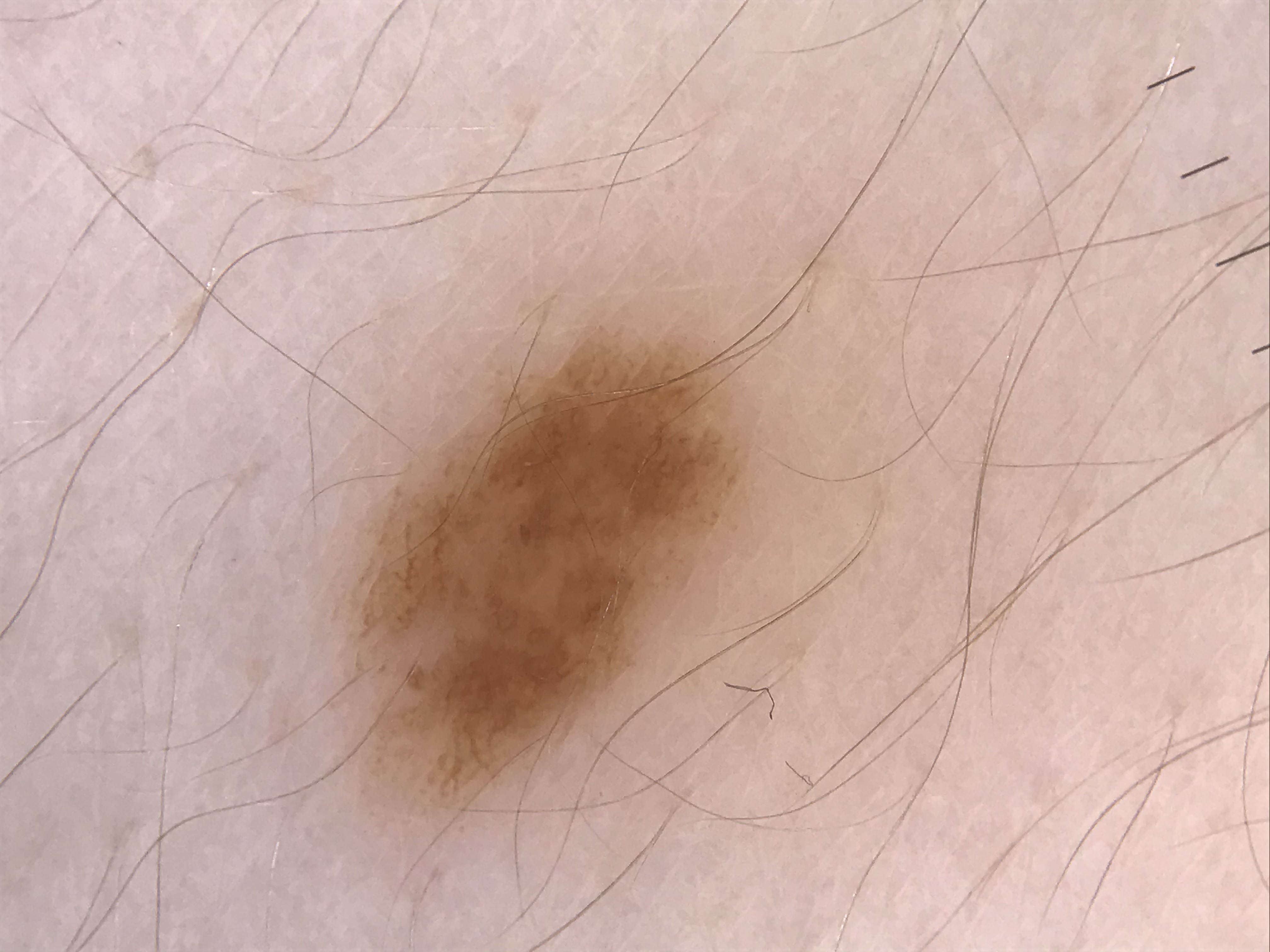Findings: A dermoscopic image of a skin lesion. Conclusion: Diagnosed as a dysplastic junctional nevus.